A dermoscopy image of a single skin lesion.
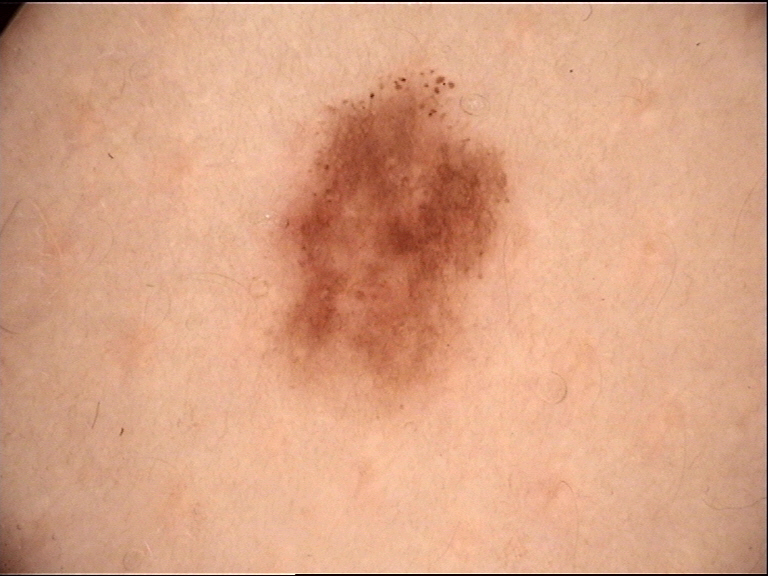Conclusion:
Classified as a dysplastic junctional nevus.